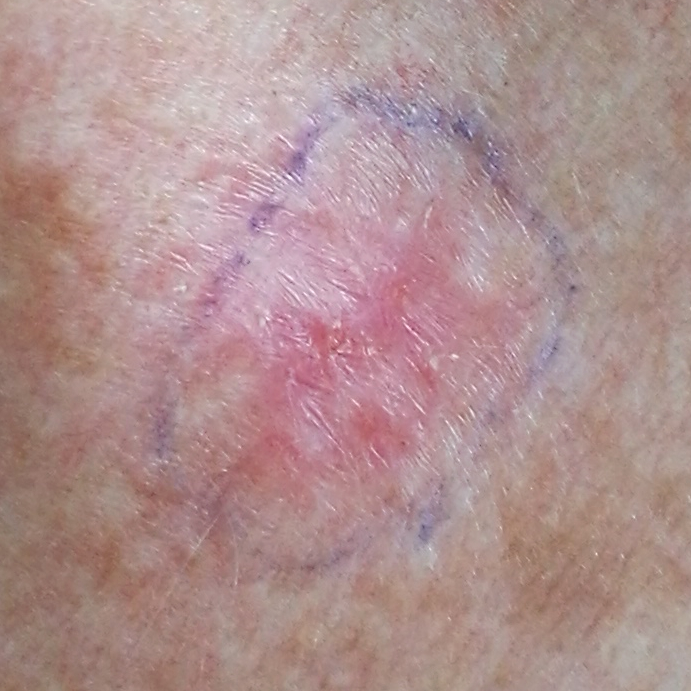subject = male, aged 33 | FST = II | modality = smartphone clinical photo | exposure history = prior malignancy (patient or family), alcohol use, pesticide exposure | location = the chest | diameter = approx. 10 × 8 mm | reported symptoms = growth, itching, bleeding, elevation / no change in appearance, no pain | diagnostic label = basal cell carcinoma (biopsy-proven).